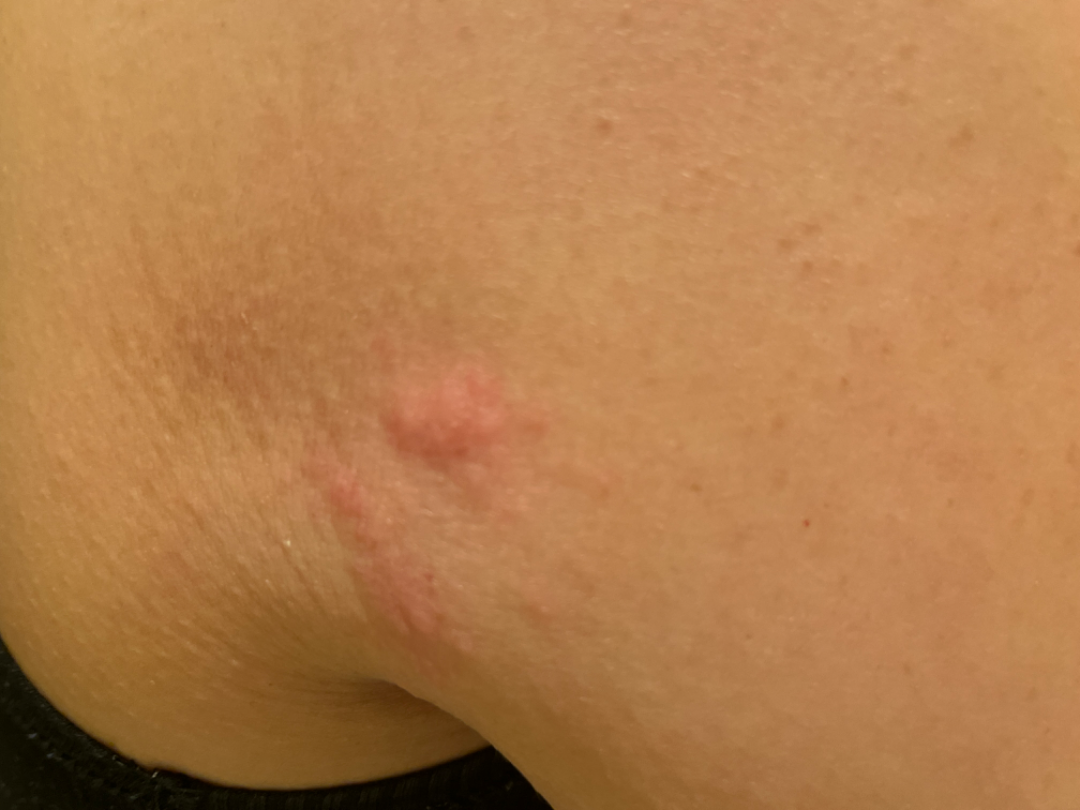differential diagnosis — most consistent with Herpes Zoster.